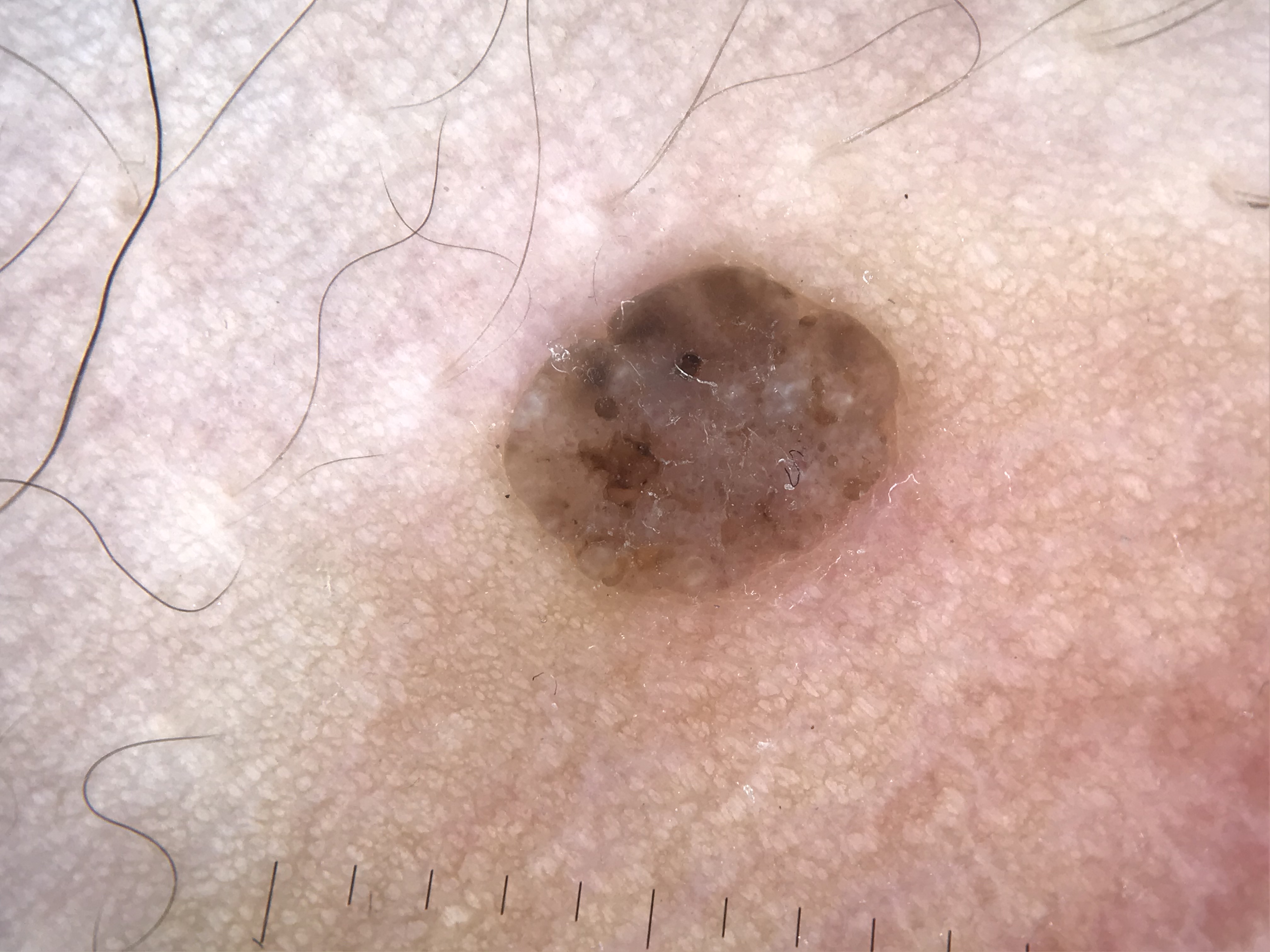Impression: Labeled as a seborrheic keratosis.